A dermoscopy image of a single skin lesion.
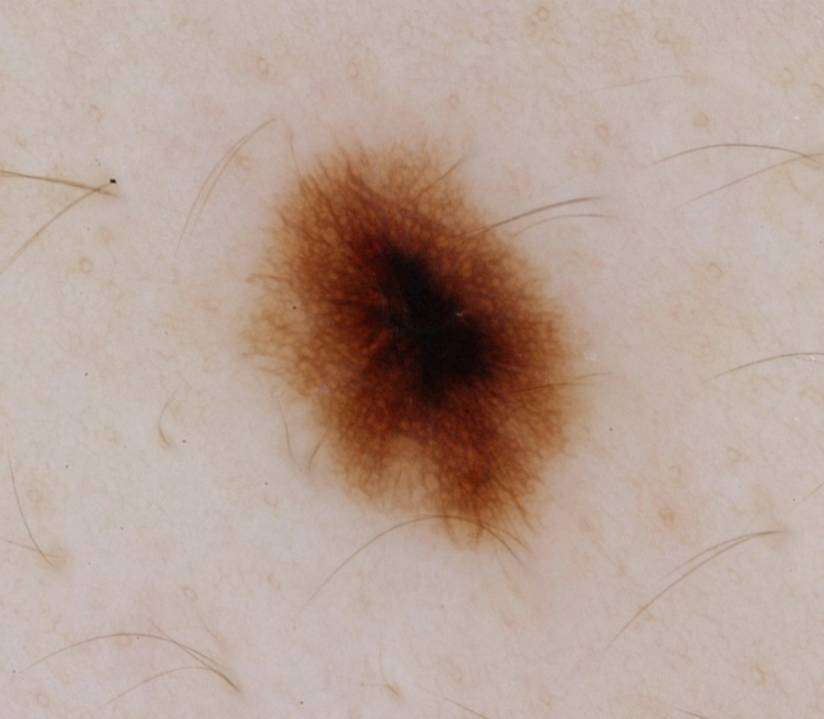Q: What dermoscopic features are present?
A: pigment network; absent: negative network, globules, streaks, and milia-like cysts
Q: What is the lesion's bounding box?
A: <box>237, 139, 590, 550</box>
Q: What did the assessment conclude?
A: a melanocytic nevus